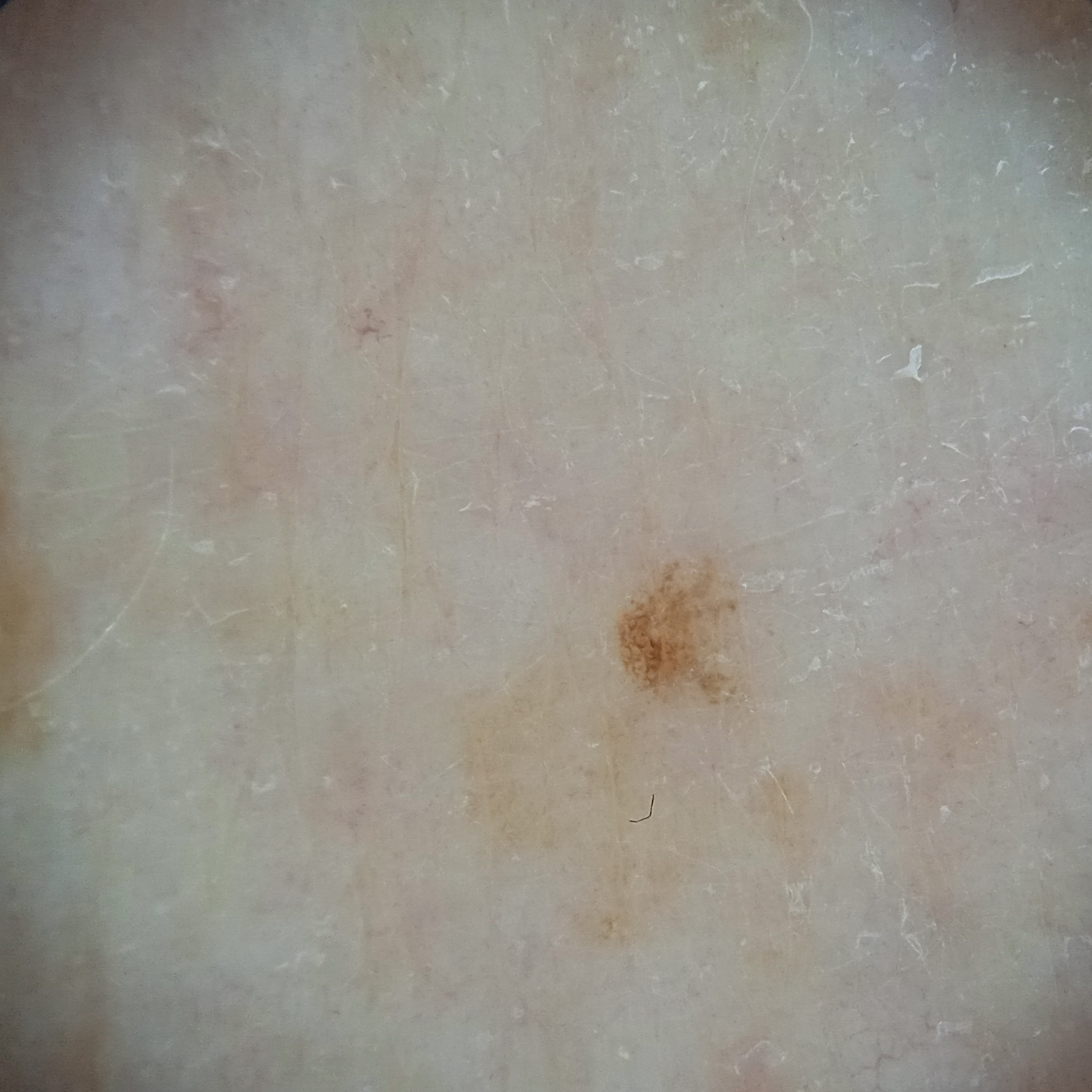referral: research study (no referral diagnosis)
patient: female, 71 years of age
nevus count: few melanocytic nevi overall
image: dermoscopy
sun reaction: skin reddens with sun exposure
relevant history: a personal history of skin cancer, a personal history of cancer, no immunosuppression, no family history of skin cancer
location: an arm
lesion size: 1.7 mm
assessment: melanocytic nevus (dermatologist consensus)